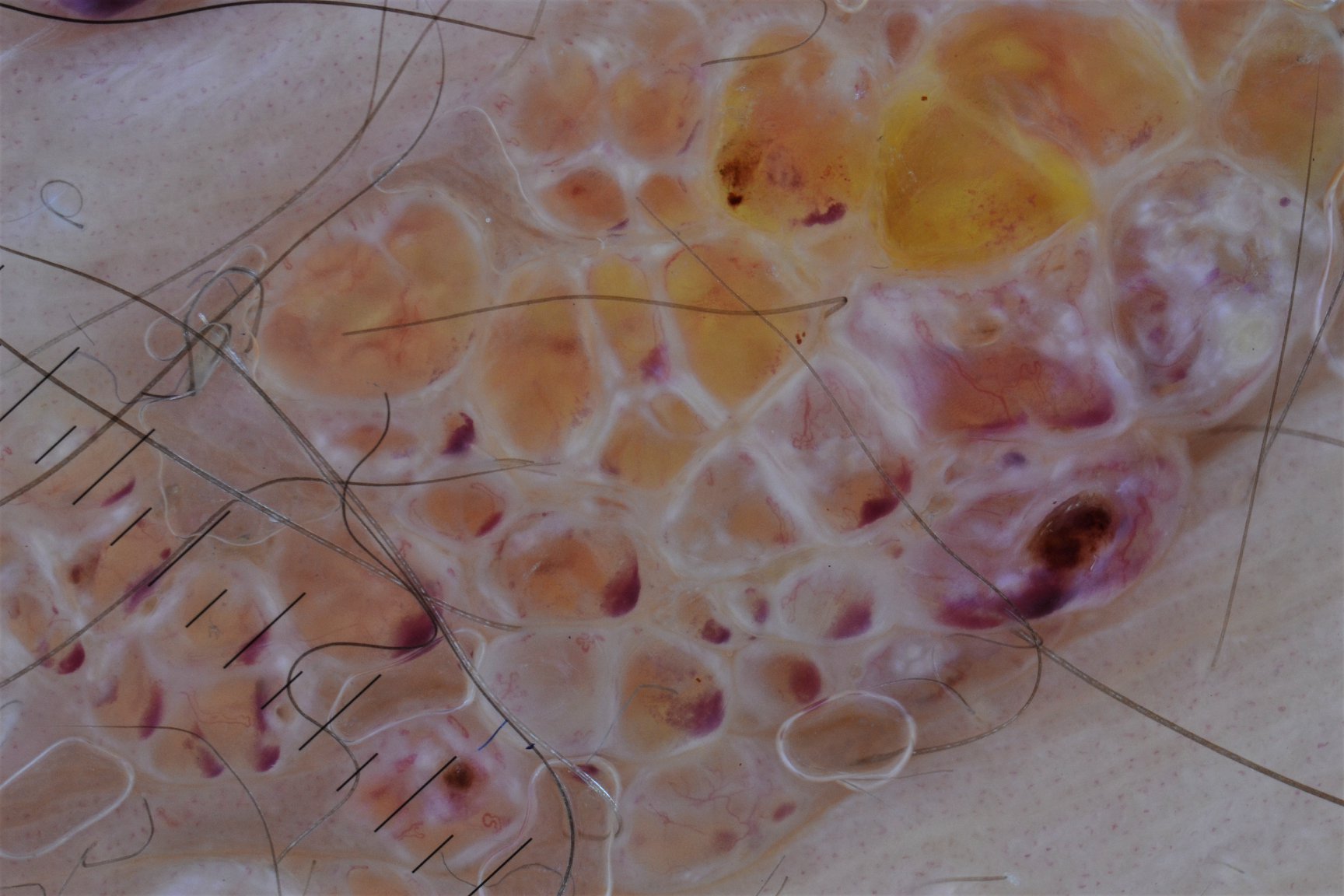{"image": "dermatoscopy", "diagnosis": {"name": "lymphangioma", "code": "la", "malignancy": "benign", "super_class": "non-melanocytic", "confirmation": "expert consensus"}}